The patient is 30–39, female. The lesion involves the head or neck and arm. The photograph was taken at a distance:
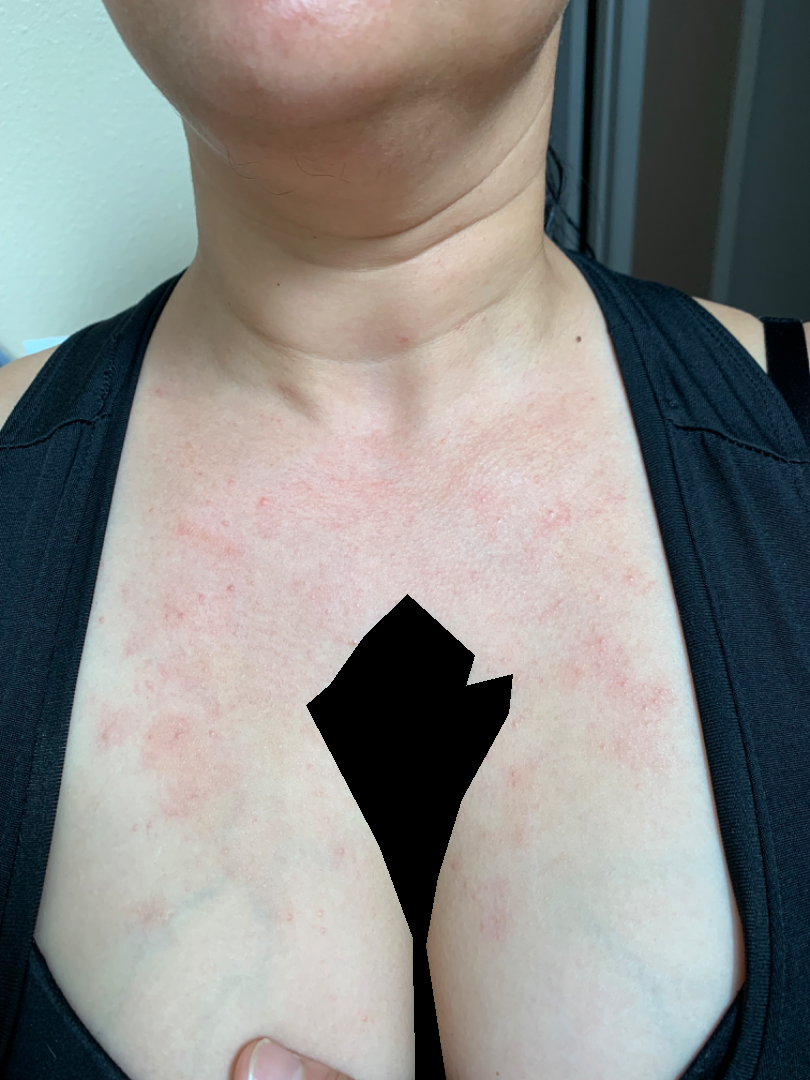Background:
Symptoms reported: burning, enlargement, itching, darkening, bothersome appearance and pain. The condition has been present for more than one year. Texture is reported as fluid-filled, flat, rough or flaky and raised or bumpy.
Findings:
On photographic review by a dermatologist, Allergic Contact Dermatitis (0.54); Photodermatitis (0.23); Folliculitis (0.23).